A dermoscopic close-up of a skin lesion:
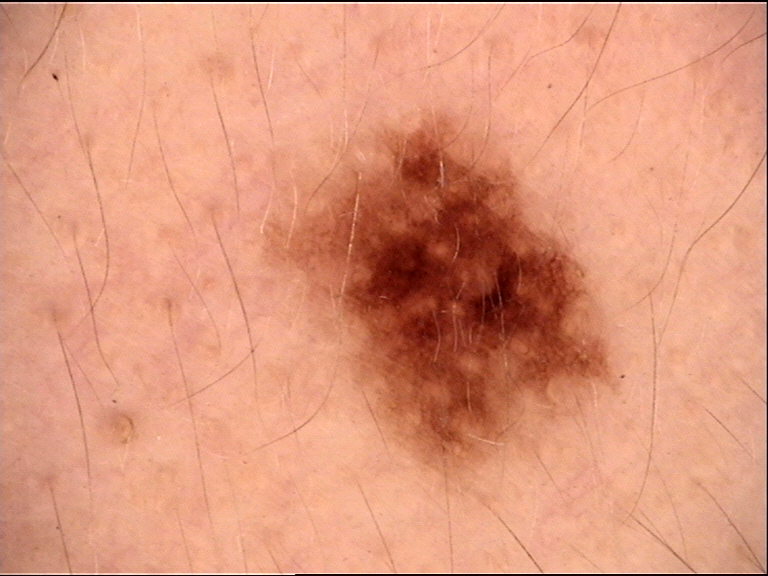assessment = dysplastic junctional nevus (expert consensus).